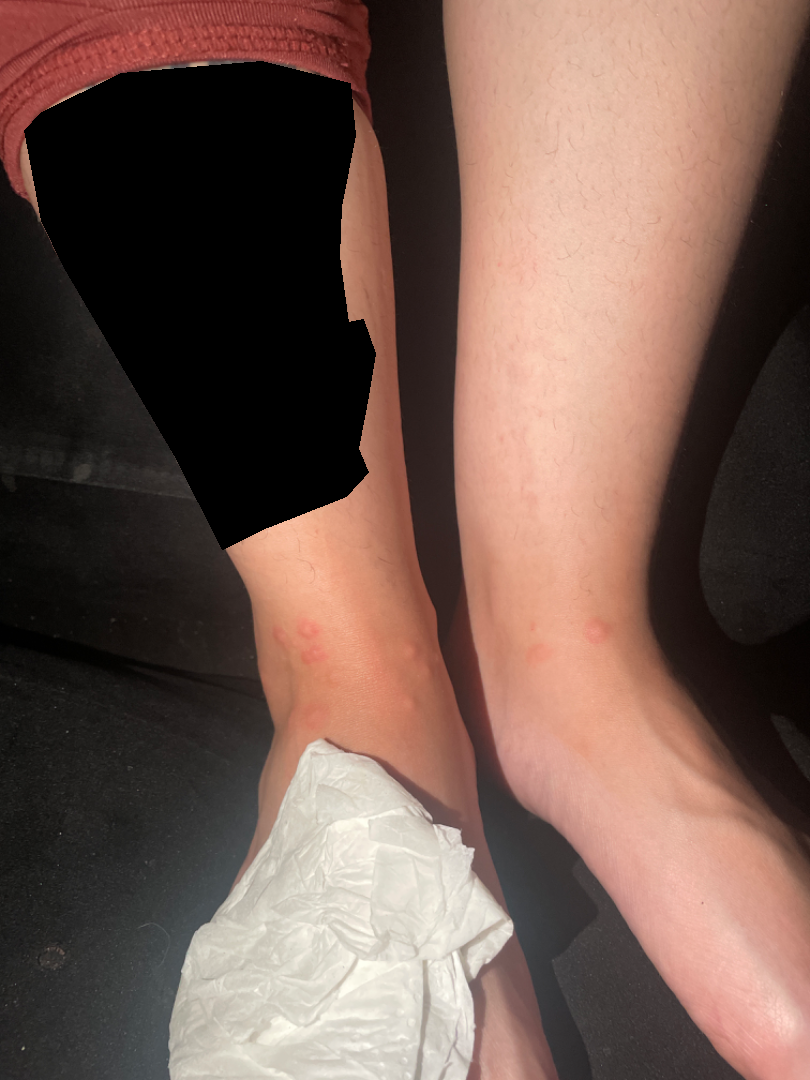The top or side of the foot is involved. The photograph was taken at a distance. Most consistent with Insect Bite.